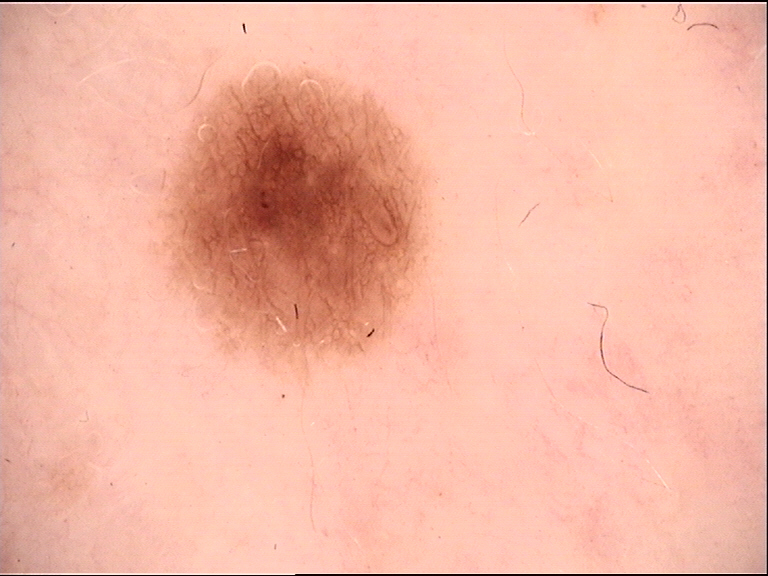Classified as a dysplastic junctional nevus.